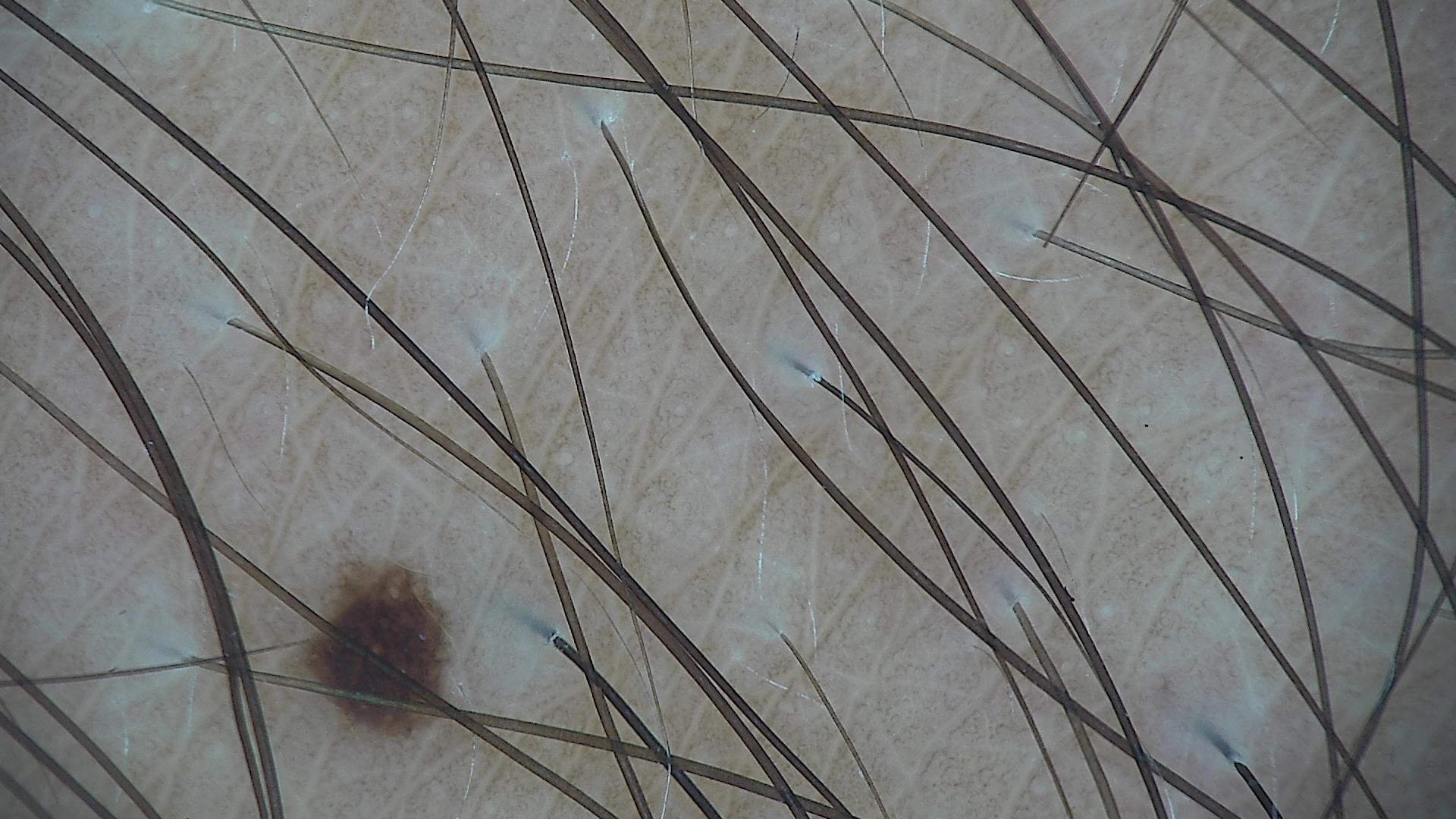Summary: A skin lesion imaged with a dermatoscope. Conclusion: The diagnosis was a dysplastic junctional nevus.